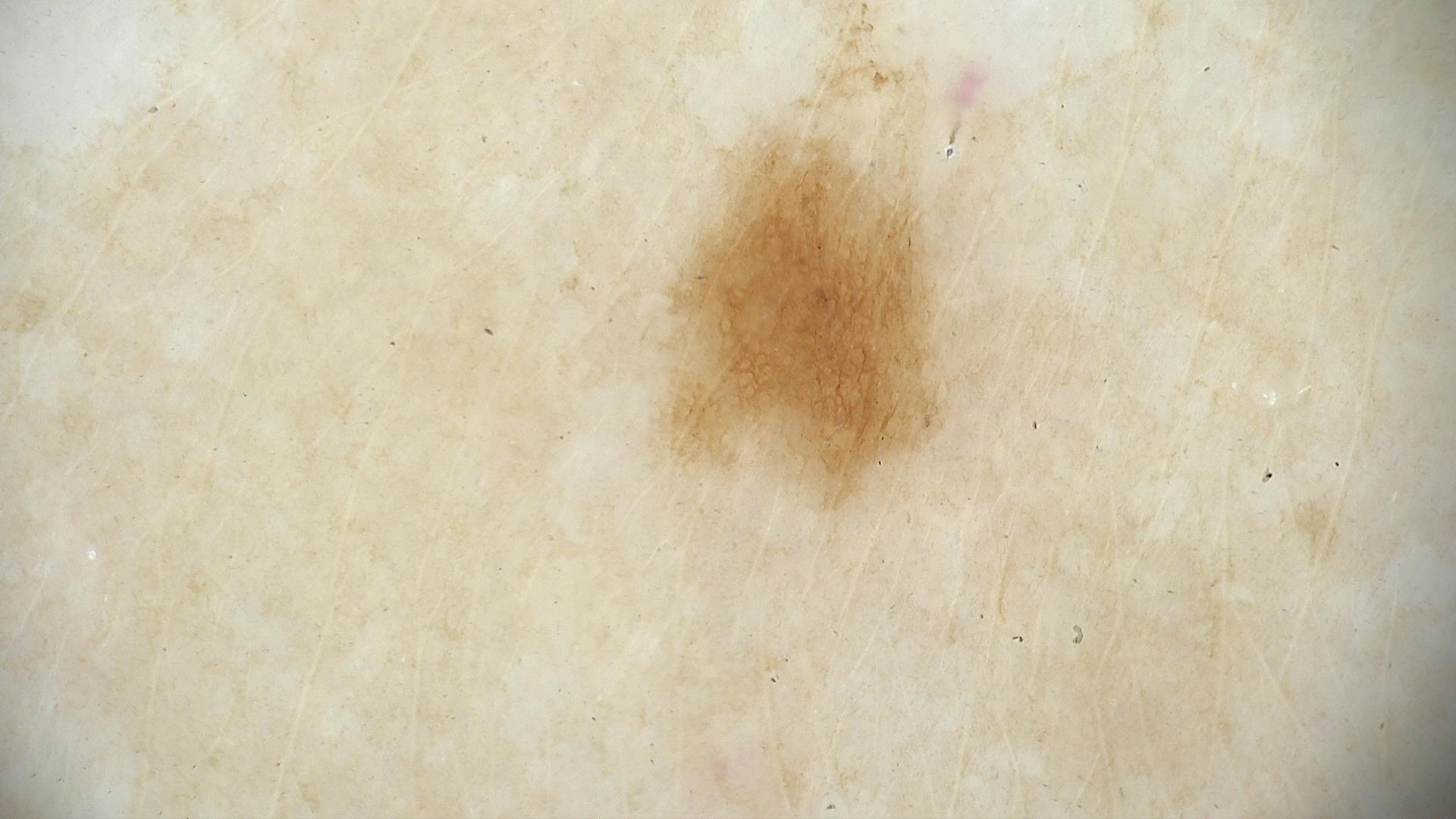Diagnosed as a benign lesion — a dysplastic junctional nevus.